The lesion involves the arm; the photograph was taken at a distance; male contributor, age 18–29: 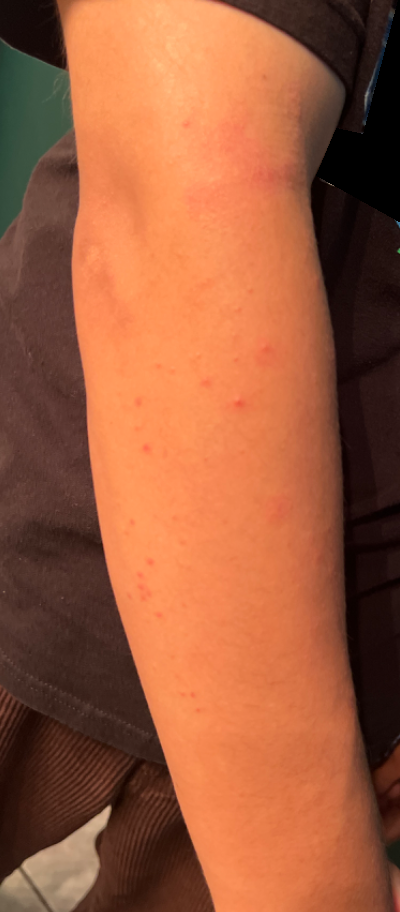Case summary:
* diagnostic considerations — the leading impression is Eczema; also consider Irritant Contact Dermatitis; less likely is Allergic Contact Dermatitis; lower on the differential is Hypersensitivity